The lesion is described as rough or flaky and raised or bumpy · the condition has been present for more than one year · the contributor is male · self-categorized by the patient as a rash · a close-up photograph · the patient reports darkening · no relevant systemic symptoms · the lesion involves the head or neck — 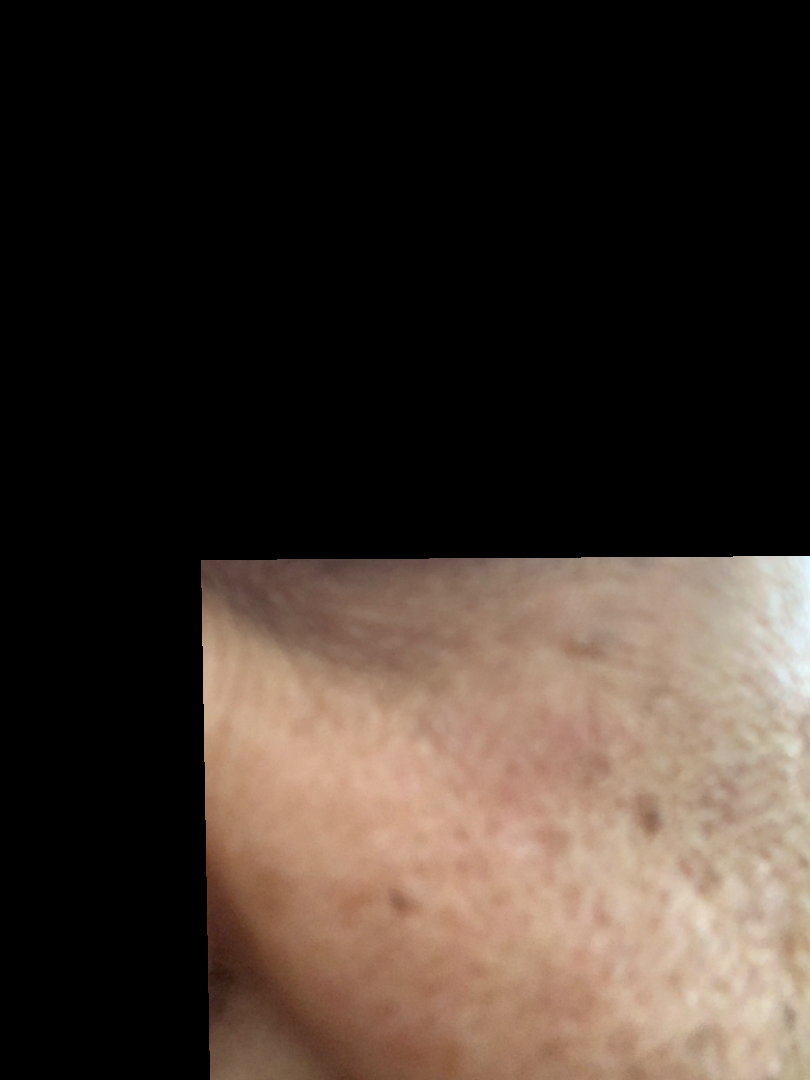assessment: unable to determine